No constitutional symptoms were reported. The patient reports the condition has been present for less than one week. Self-categorized by the patient as a rash. The lesion is described as raised or bumpy. The lesion involves the arm and front of the torso. The photograph was taken at a distance. The lesion is associated with bothersome appearance:
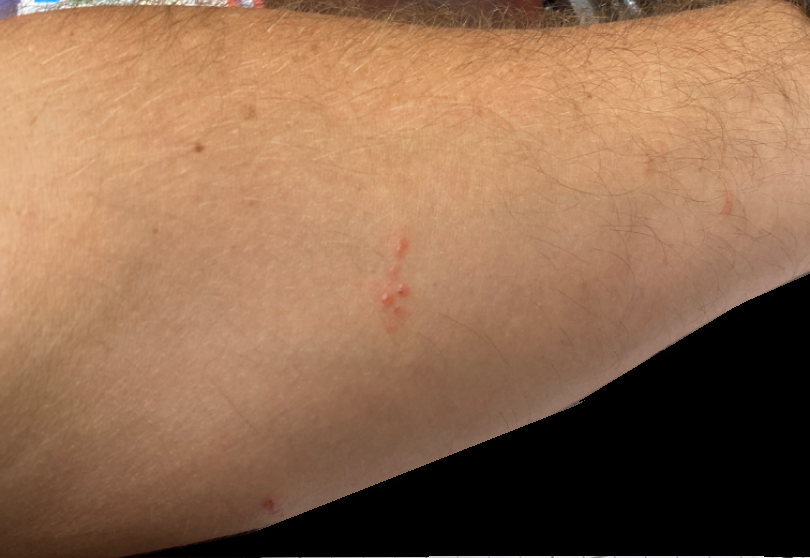The skin condition could not be confidently assessed from this image.